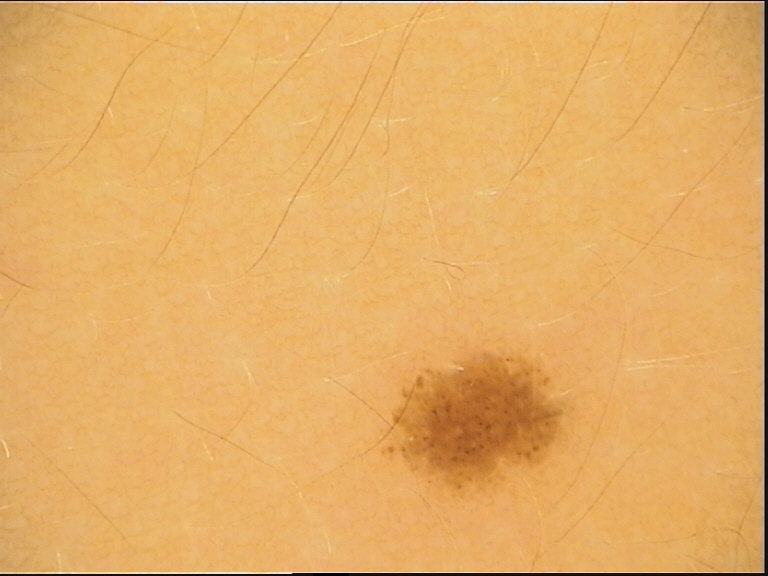Conclusion:
The diagnostic label was a dysplastic junctional nevus.